The contributor reports the condition has been present for about one day; the leg is involved; the patient also reports fatigue; self-categorized by the patient as a rash; reported lesion symptoms include burning, itching and bothersome appearance; a close-up photograph.
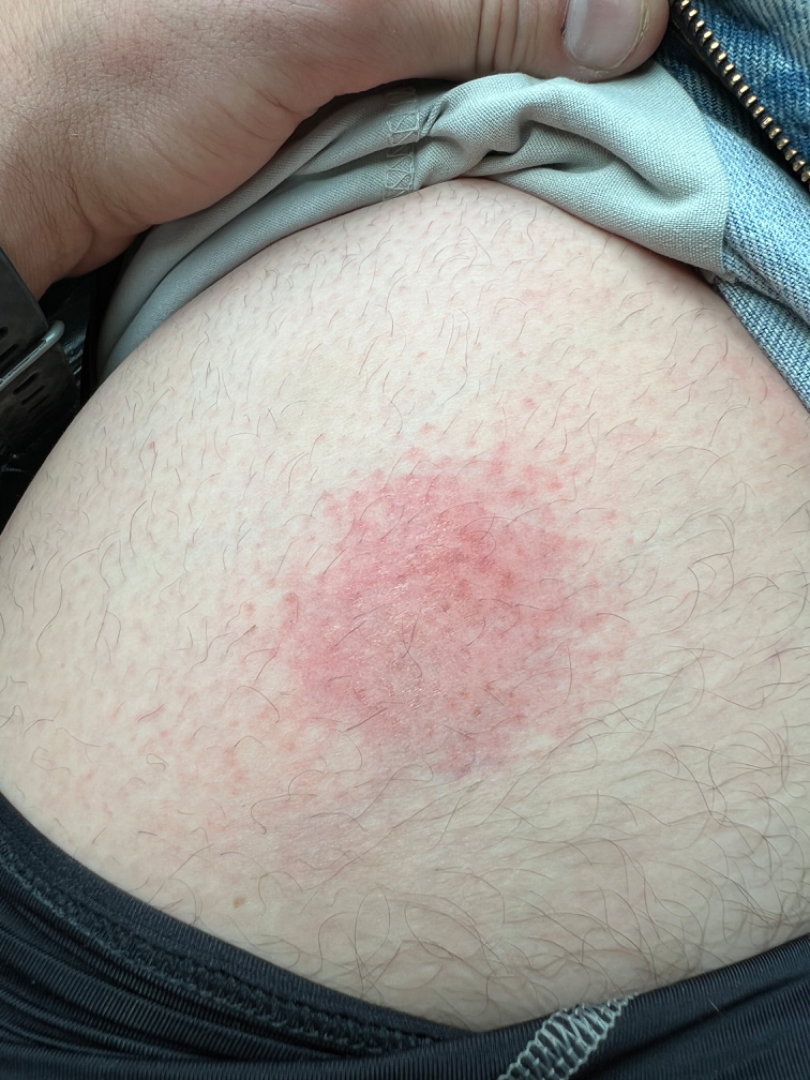On dermatologist assessment of the image: most likely Eczema; the differential also includes Allergic Contact Dermatitis; a remote consideration is Psoriasis.